A dermoscopic image of a skin lesion:
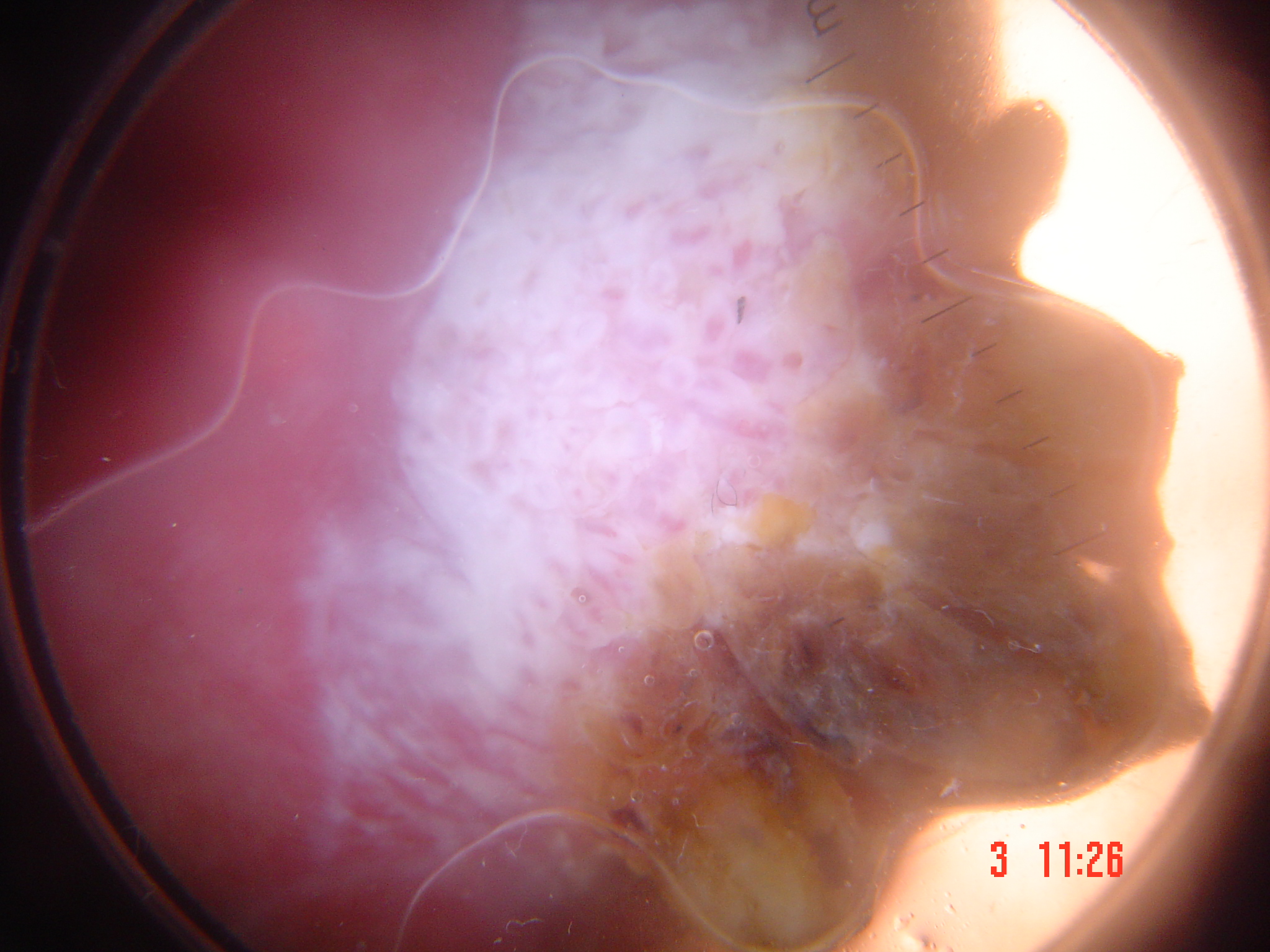diagnostic label = squamous cell carcinoma (biopsy-proven).